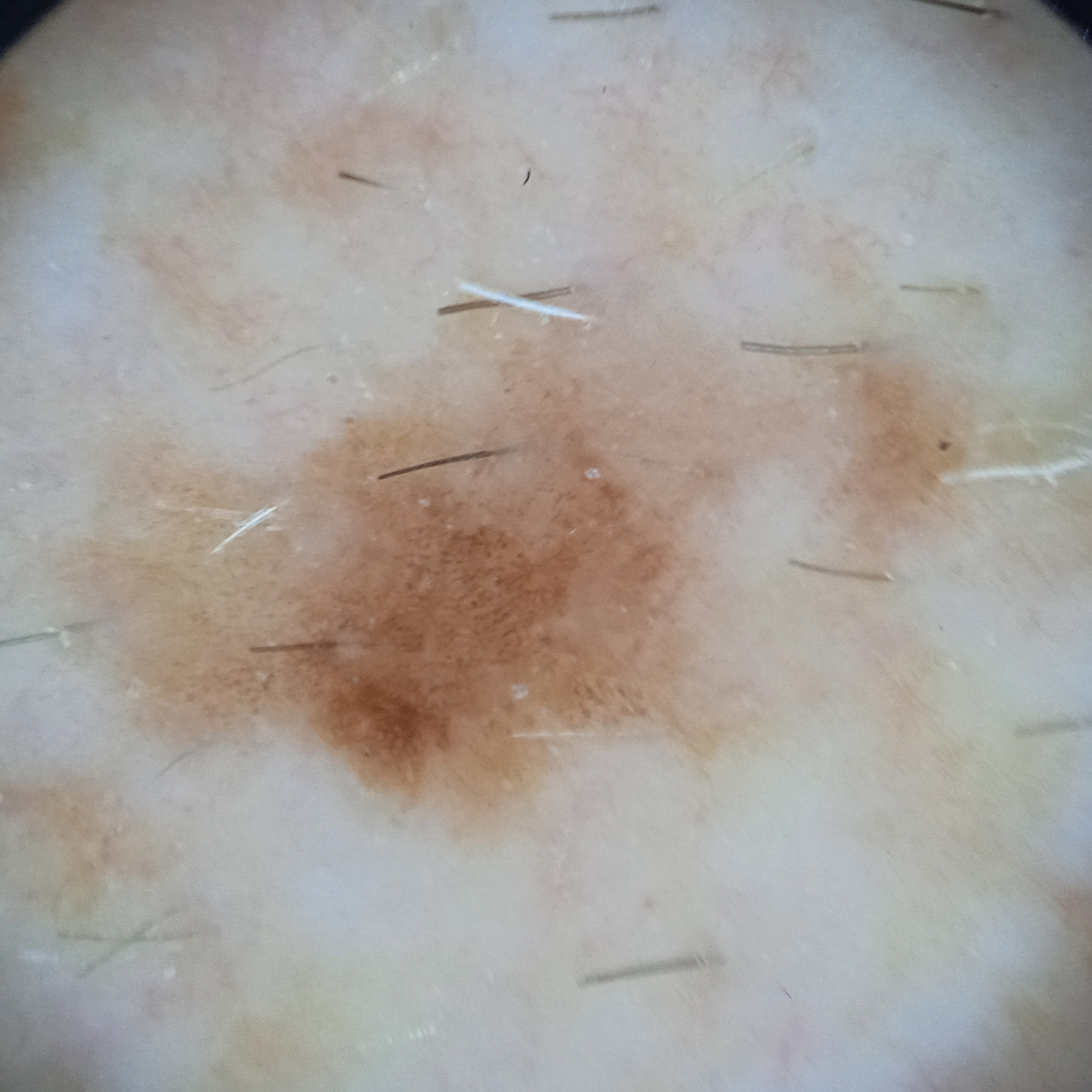The patient describes having numerous moles.
Collected as part of a research study, without a referral diagnosis.
A male patient age 73.
On a questionnaire the patient reported a personal history of cancer, no personal history of skin cancer, and no family history of skin cancer.
The lesion is located on the torso.
Measuring roughly 6.6 mm.
Reviewed by four dermatologists, the consensus diagnosis was a melanoma; the reviewers were not unanimous; the differential also included a solar lentigo, seborrheic keratosis, or atypical nevus.